The patient says their skin reddens painfully with sun exposure · acquired for a research image collection, with no referral diagnosis · a female patient aged 35 · the patient describes having a moderate number of moles — 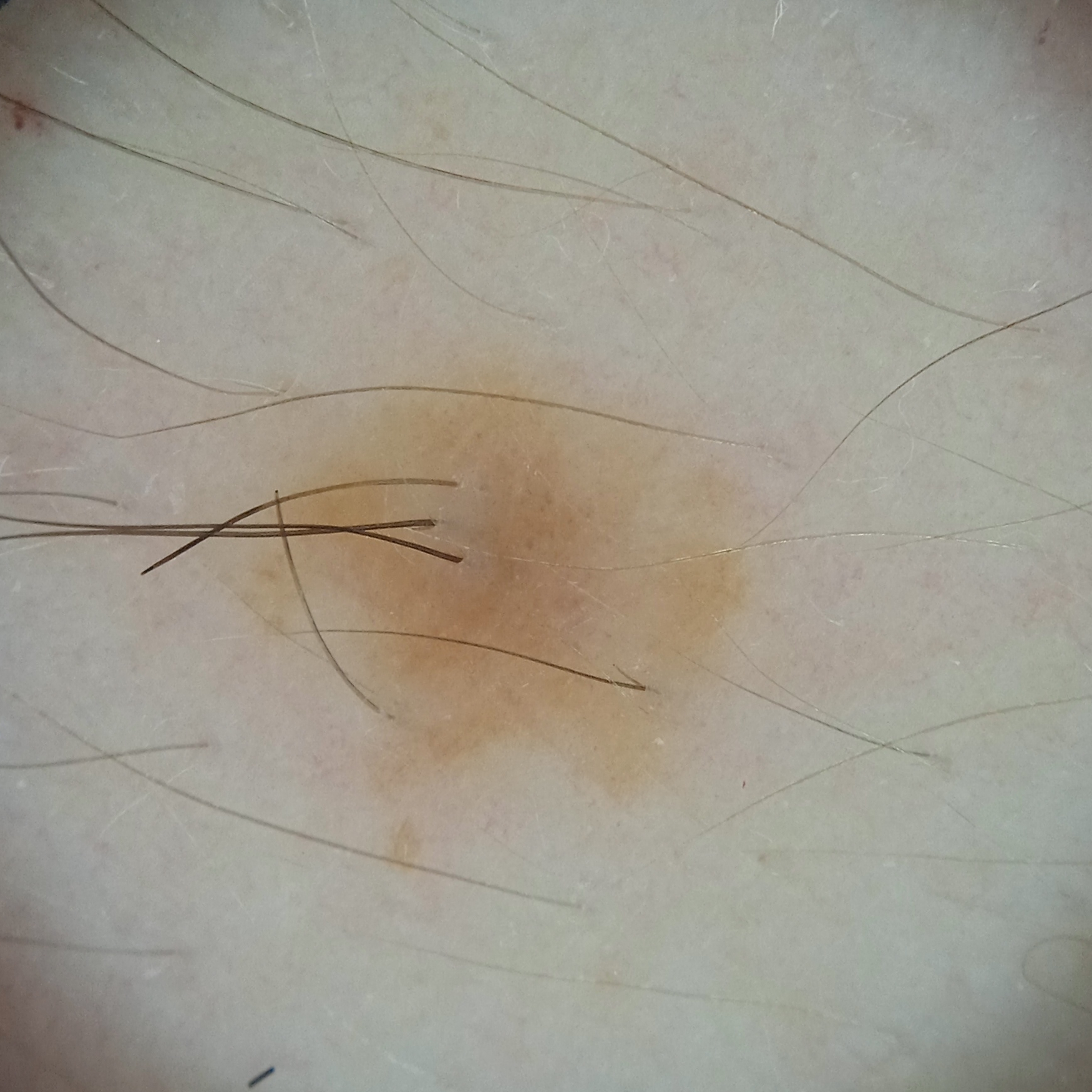Located on an arm. The lesion measures approximately 5.8 mm. On independent review by four dermatologists, the agreed diagnosis was a melanocytic nevus; the reviewers were not unanimous; diagnostic confidence was moderate.